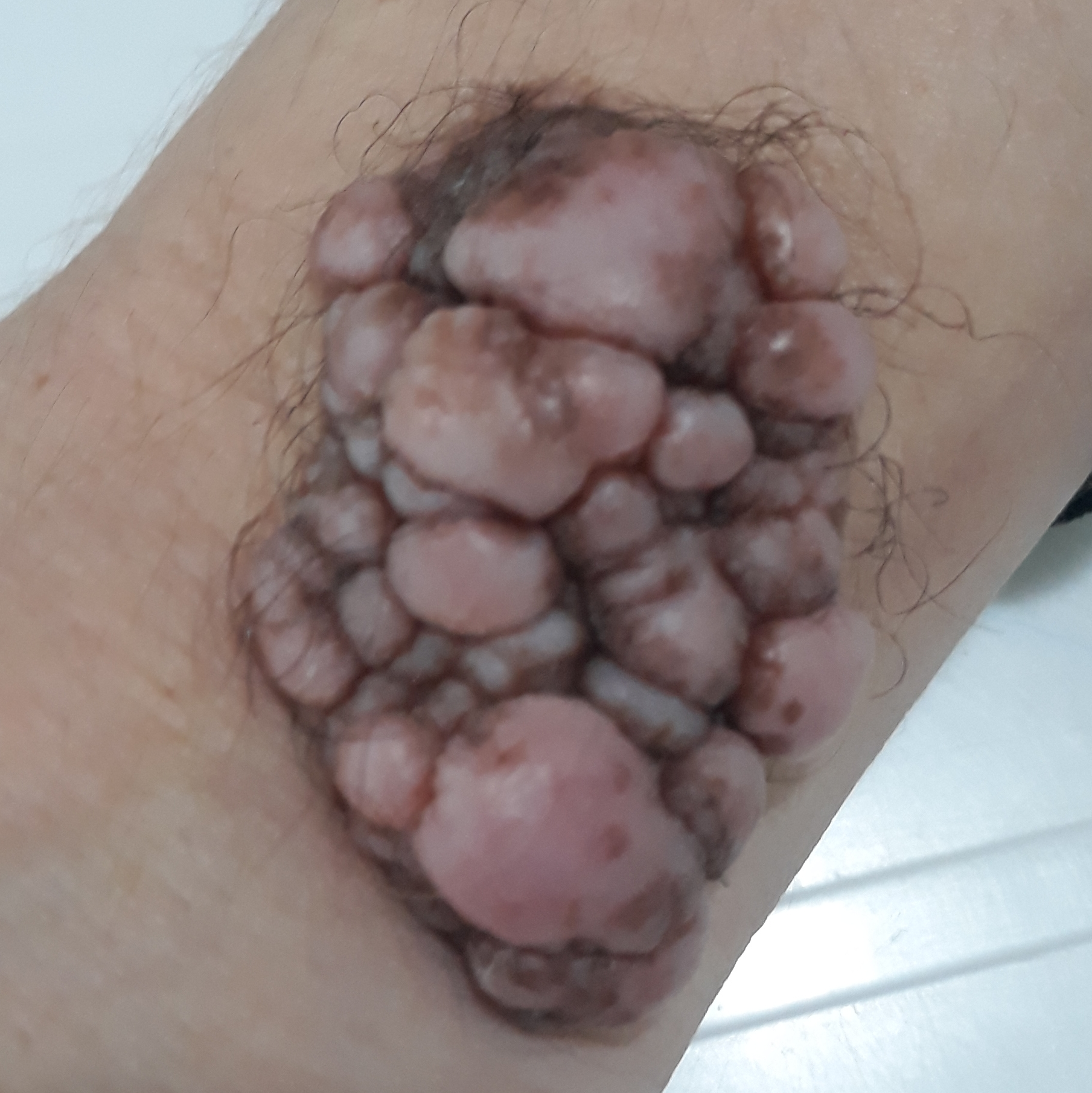A clinical close-up photograph of a skin lesion. The lesion is located on a forearm. The patient reports that the lesion has grown, is elevated, and has changed. Expert review favored a nevus.